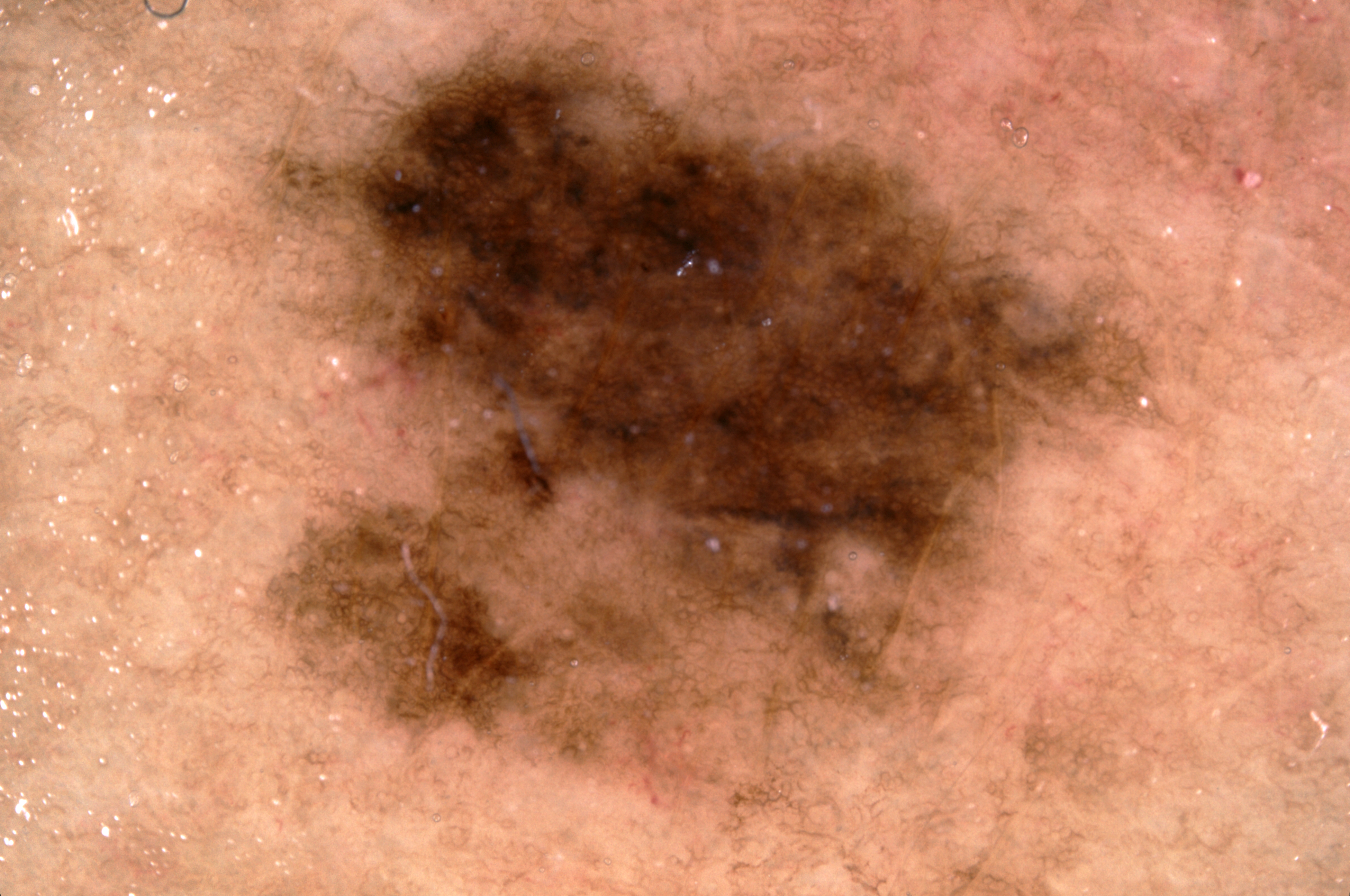Summary: A skin lesion imaged with a dermatoscope. A male patient aged 83 or over. Dermoscopy demonstrates pigment network, with no milia-like cysts, negative network, or streaks. In (x1, y1, x2, y2) order, the lesion's extent is box(245, 0, 1165, 831). Conclusion: Diagnosed as a melanocytic nevus.